The chart records a previous melanoma · the patient was assessed as Fitzpatrick II · contact-polarized dermoscopy of a skin lesion.
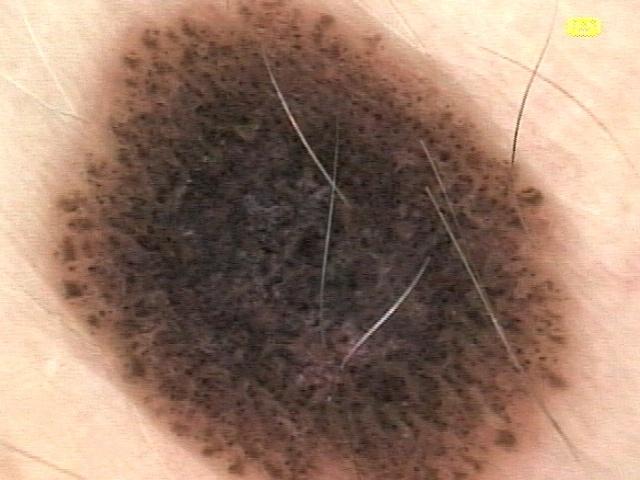Located on the trunk. Confirmed on histopathology as a malignant lesion — a melanoma.